A female patient, aged around 30 · this is a dermoscopic photograph of a skin lesion.
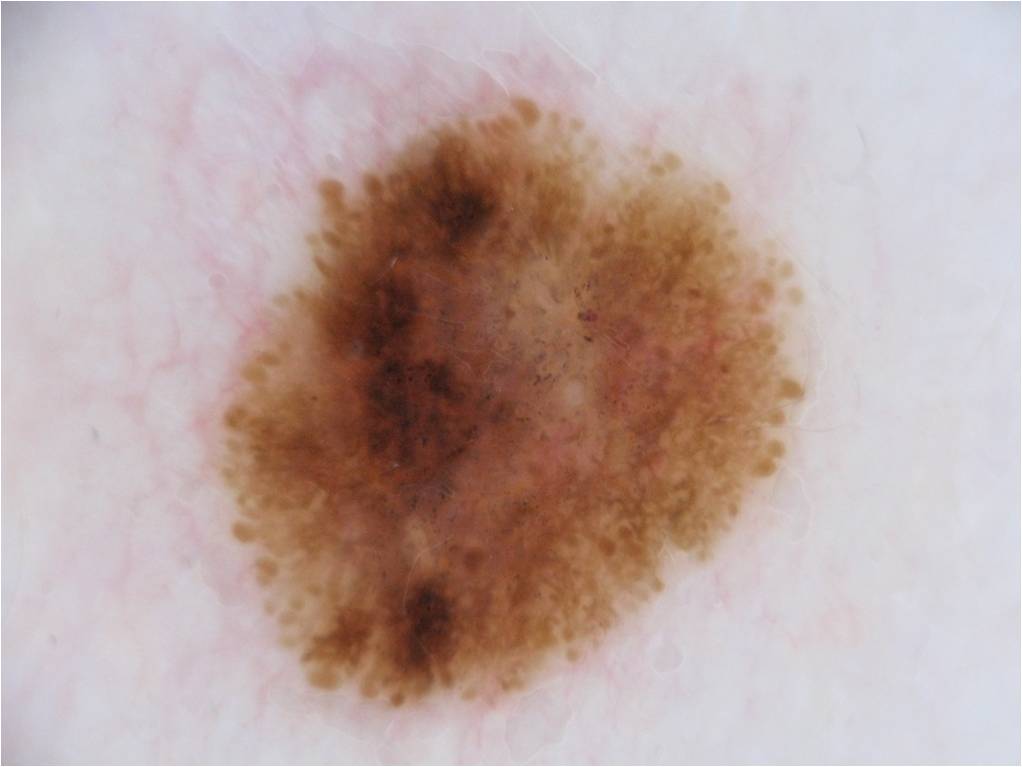* features — globules, pigment network, and streaks; absent: milia-like cysts and negative network
* lesion bbox — 200/85/806/713
* impression — a melanocytic nevus